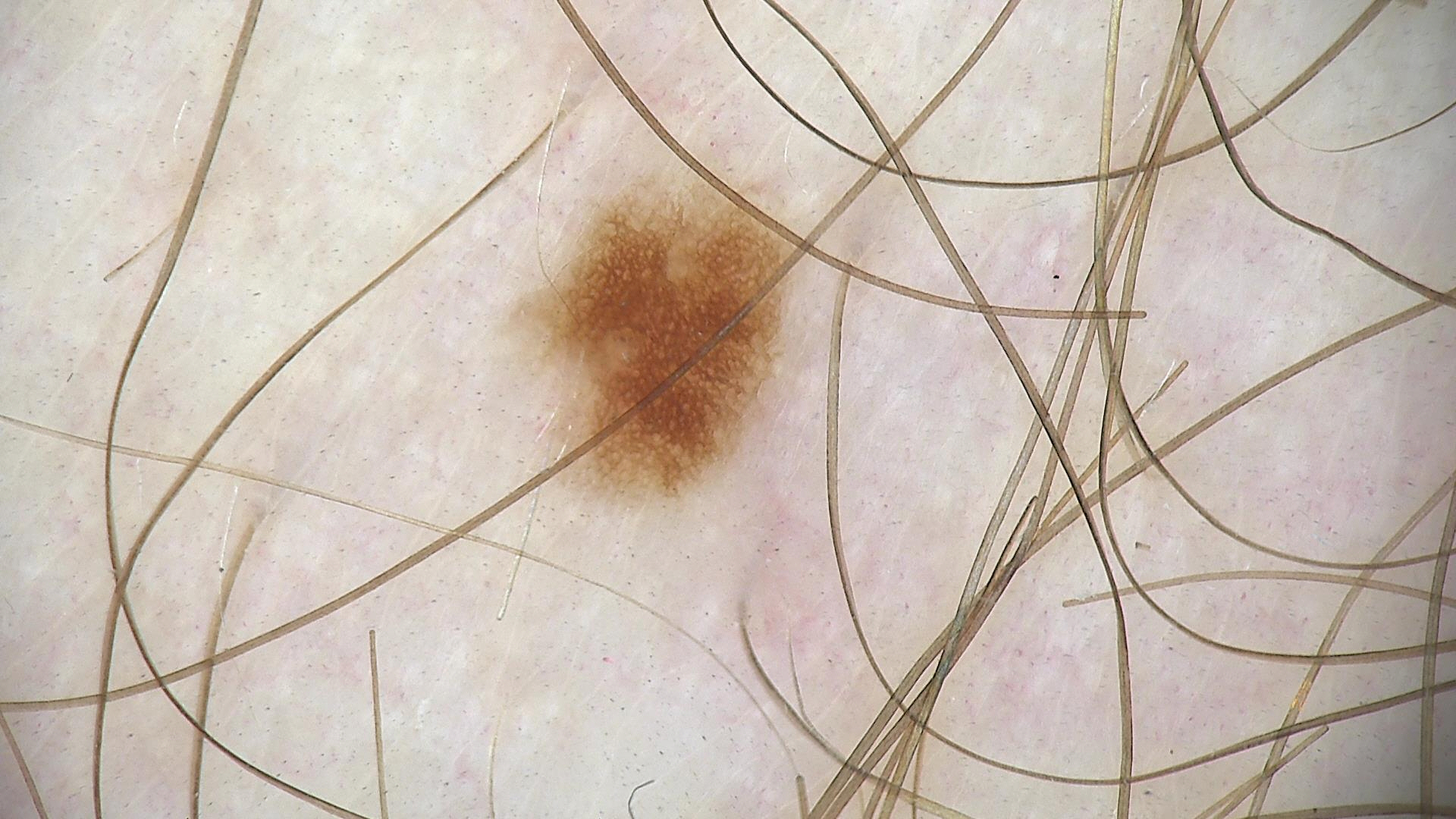A dermoscopy image of a single skin lesion. Labeled as a benign lesion — a dysplastic junctional nevus.